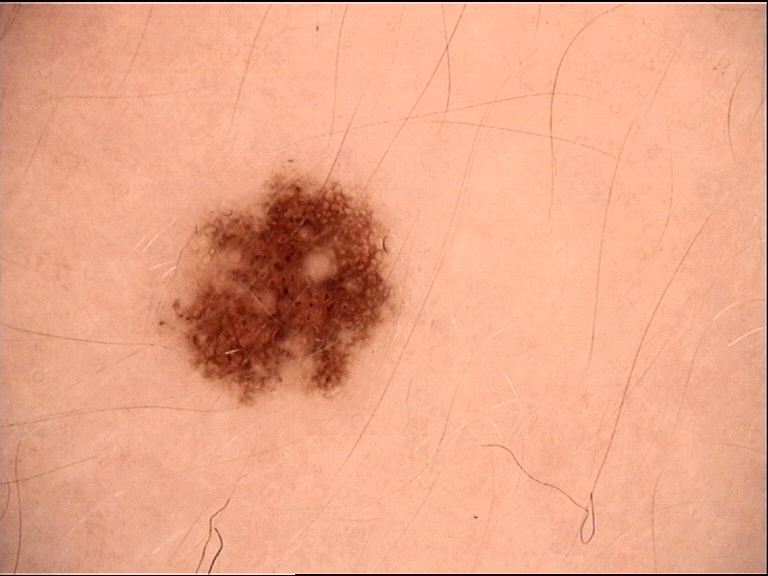A dermoscopy image of a single skin lesion. Diagnosed as a dysplastic junctional nevus.